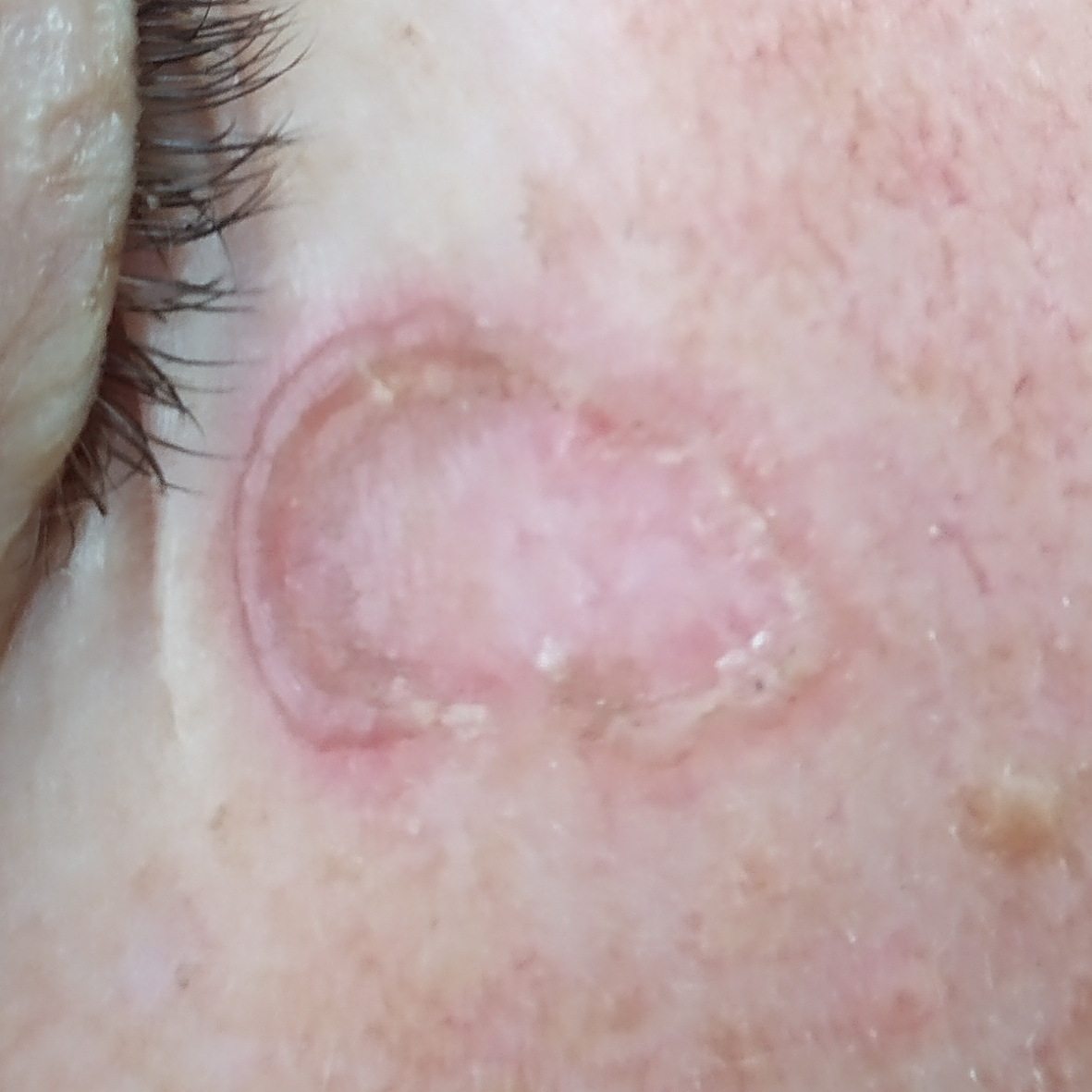Diagnosis:
Histopathological examination showed an actinic keratosis.